A dermoscopic close-up of a skin lesion: 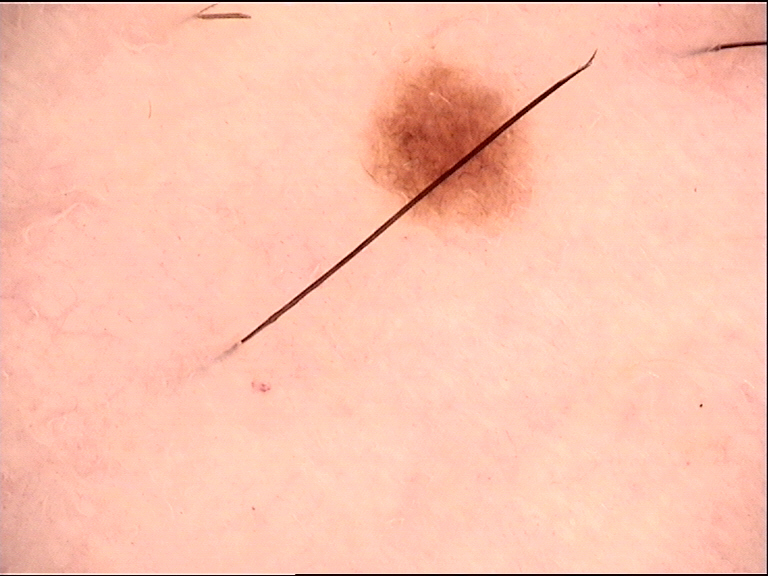label = dysplastic junctional nevus (expert consensus).